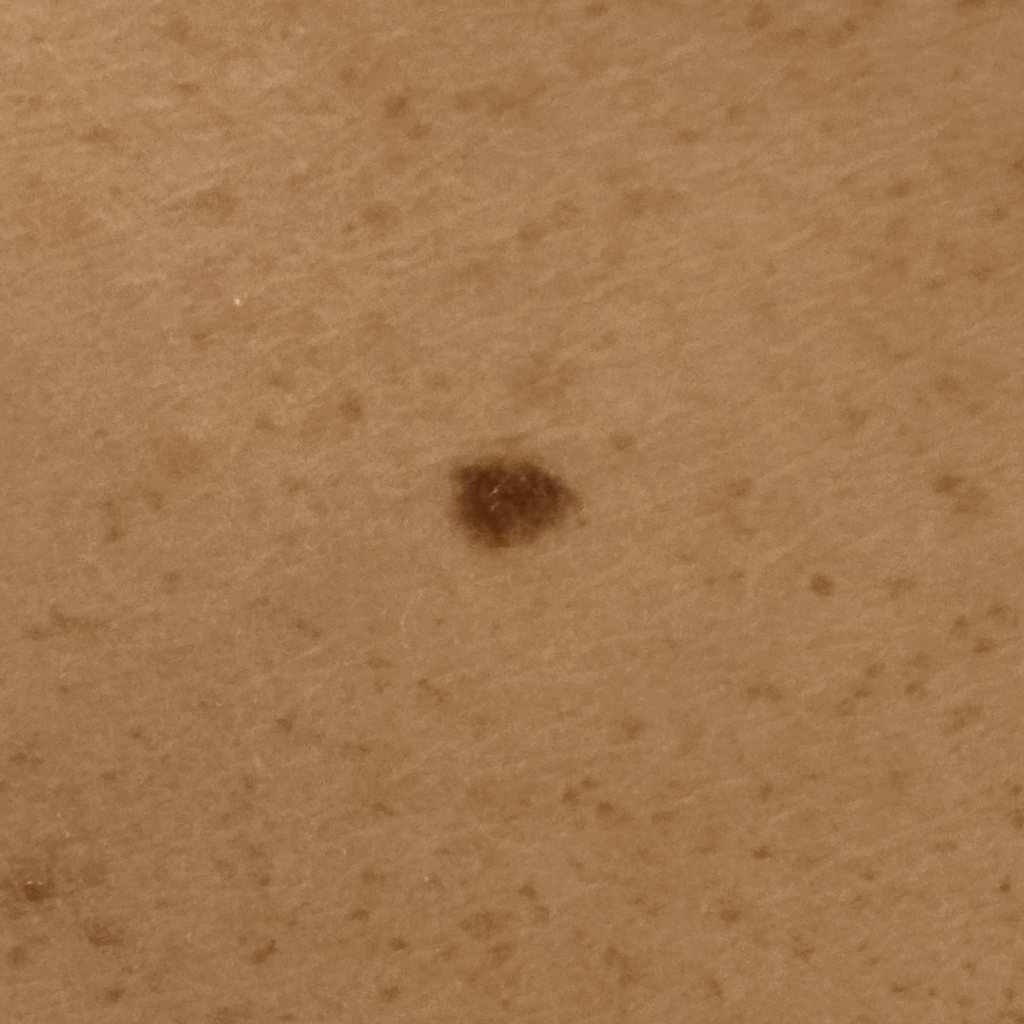The dermatologists' assessment was a melanocytic nevus.